The photograph is a close-up of the affected area: 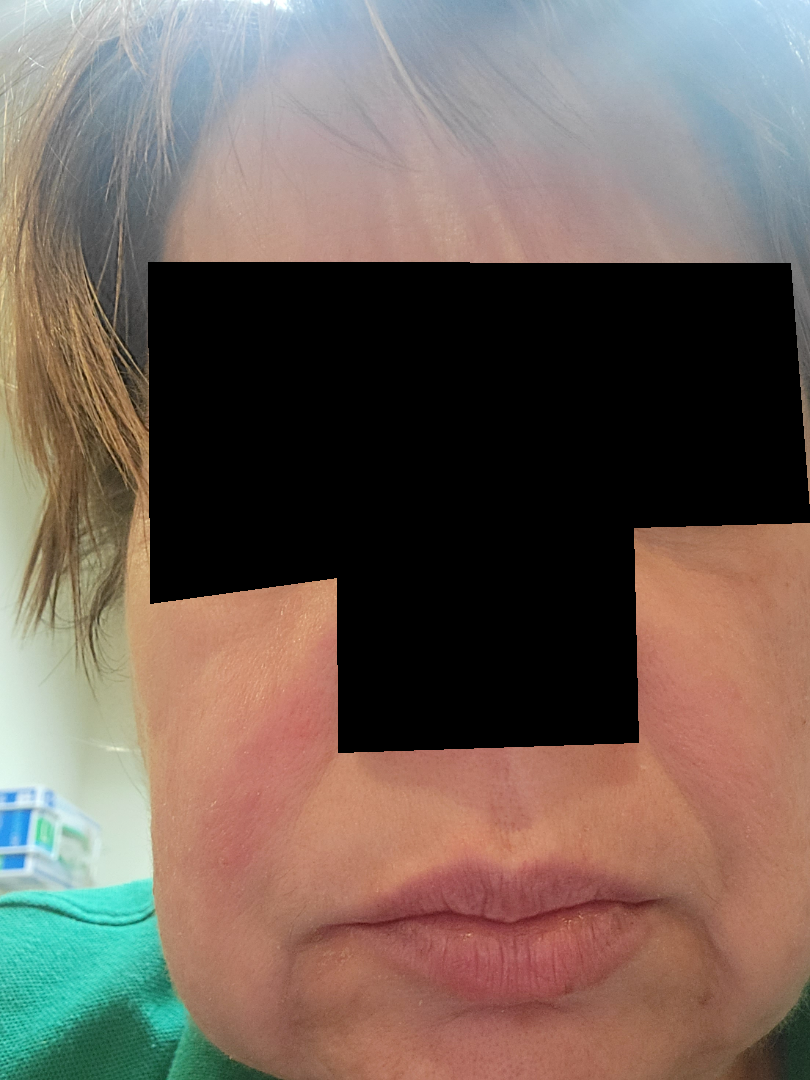On dermatologist assessment of the image, the differential is split between Irritant Contact Dermatitis and Seborrheic Dermatitis; a remote consideration is Allergic Contact Dermatitis.